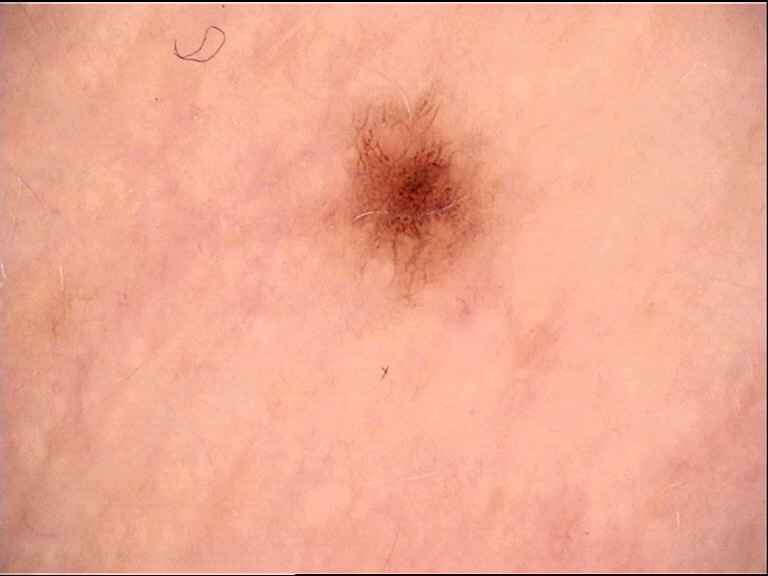A skin lesion imaged with a dermatoscope. Diagnosed as a dysplastic junctional nevus.